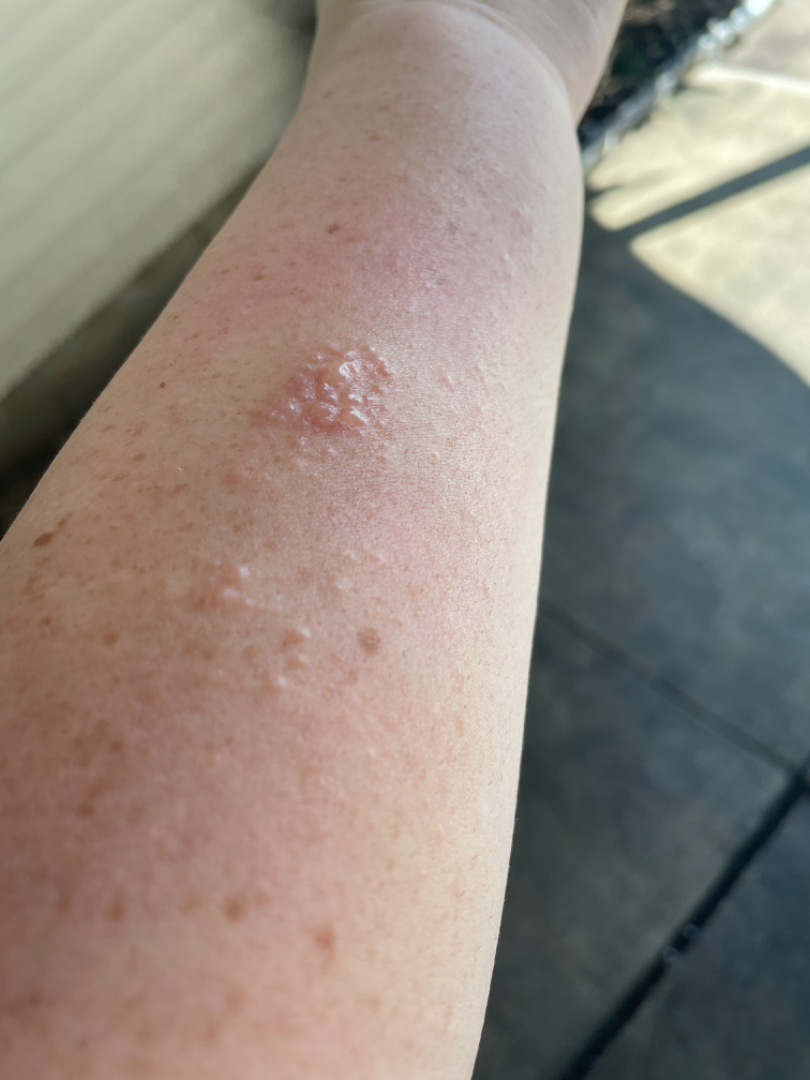• anatomic site: arm
• patient: female, age 30–39
• image framing: at a distance
• self-categorized as: a rash
• skin tone: FST I; lay reviewers estimated MST 3 or 4
• associated systemic symptoms: fatigue
• surface texture: fluid-filled and raised or bumpy
• duration: less than one week
• differential: most likely Herpes Simplex; also raised was Allergic Contact Dermatitis; with consideration of Herpes Zoster; less likely is Lymphangioma